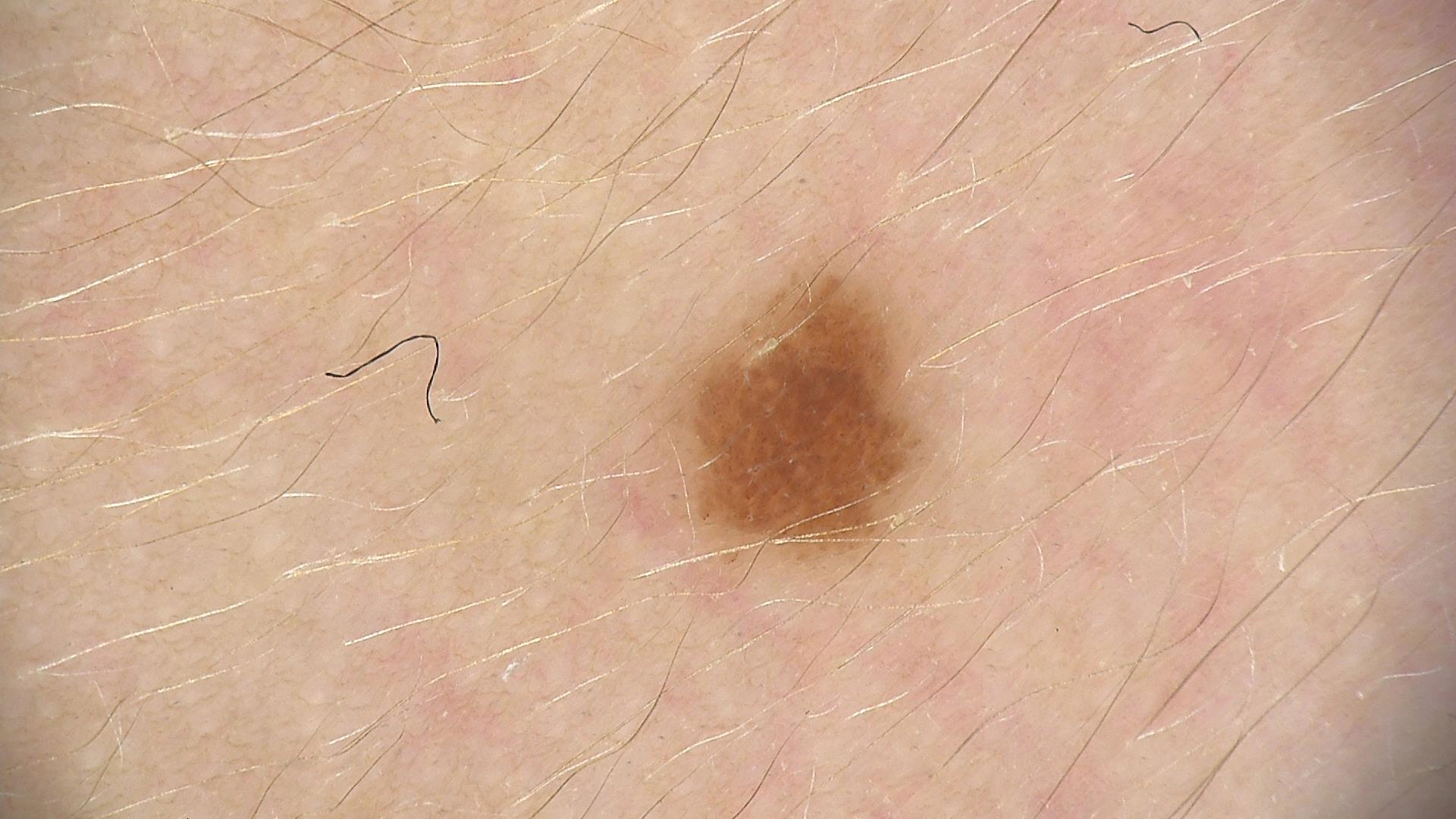Findings: A dermatoscopic image of a skin lesion. The architecture is that of a banal lesion. Impression: The diagnosis was a junctional nevus.